Few moles overall by the patient's own estimate; dermoscopy of a skin lesion; acquired for a research image collection, with no referral diagnosis: 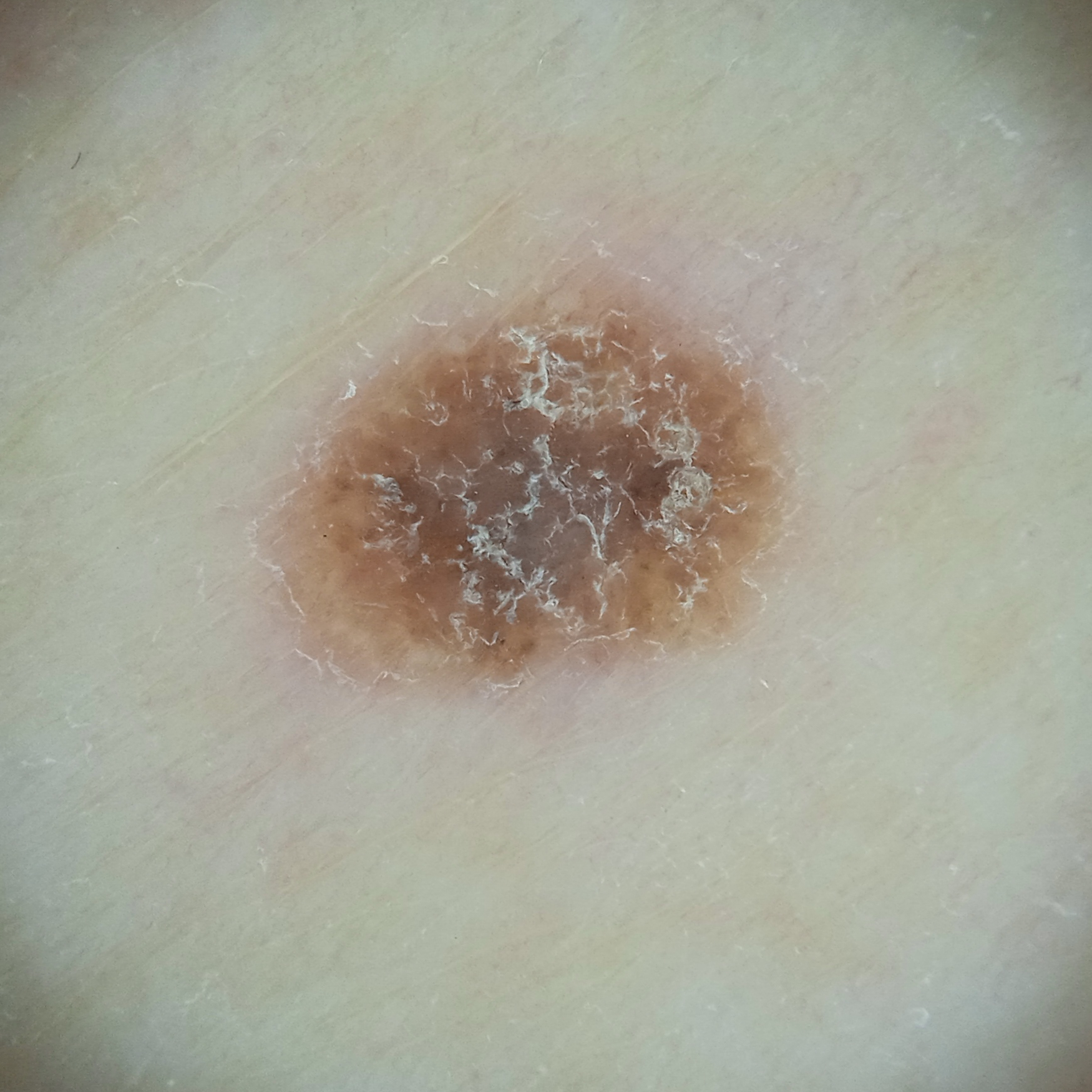Dermatologist review favored a seborrheic keratosis.